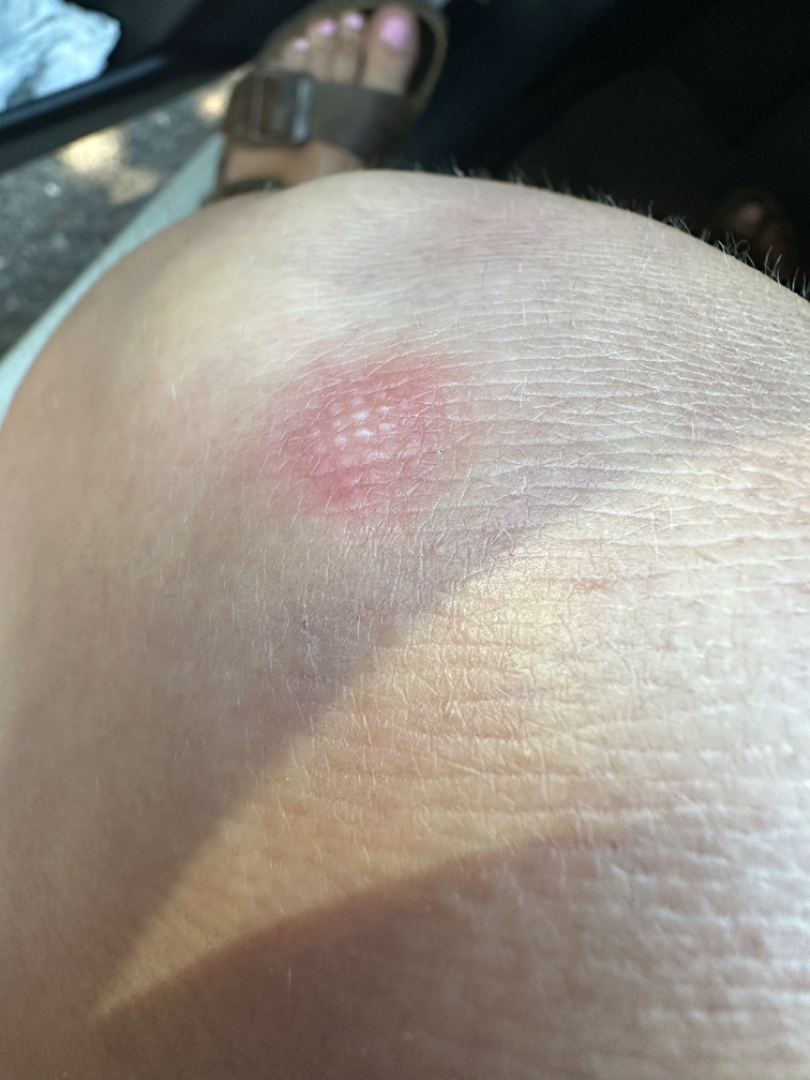The case was difficult to assess from the available photograph. An image taken at an angle.